Female contributor, age 40–49 · an image taken at a distance · located on the leg — 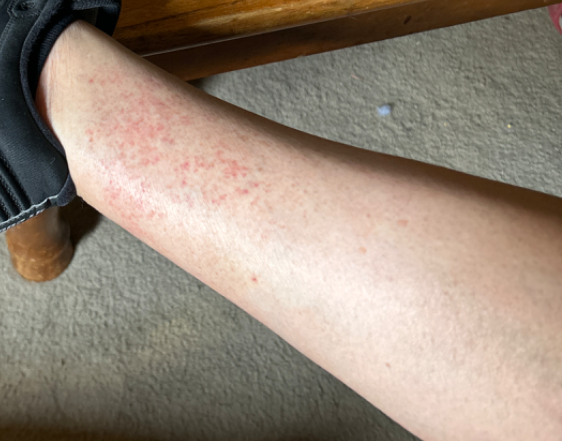Pigmented purpuric eruption and Leukocytoclastic Vasculitis were considered with similar weight.